FST II; a female patient aged approximately 20: 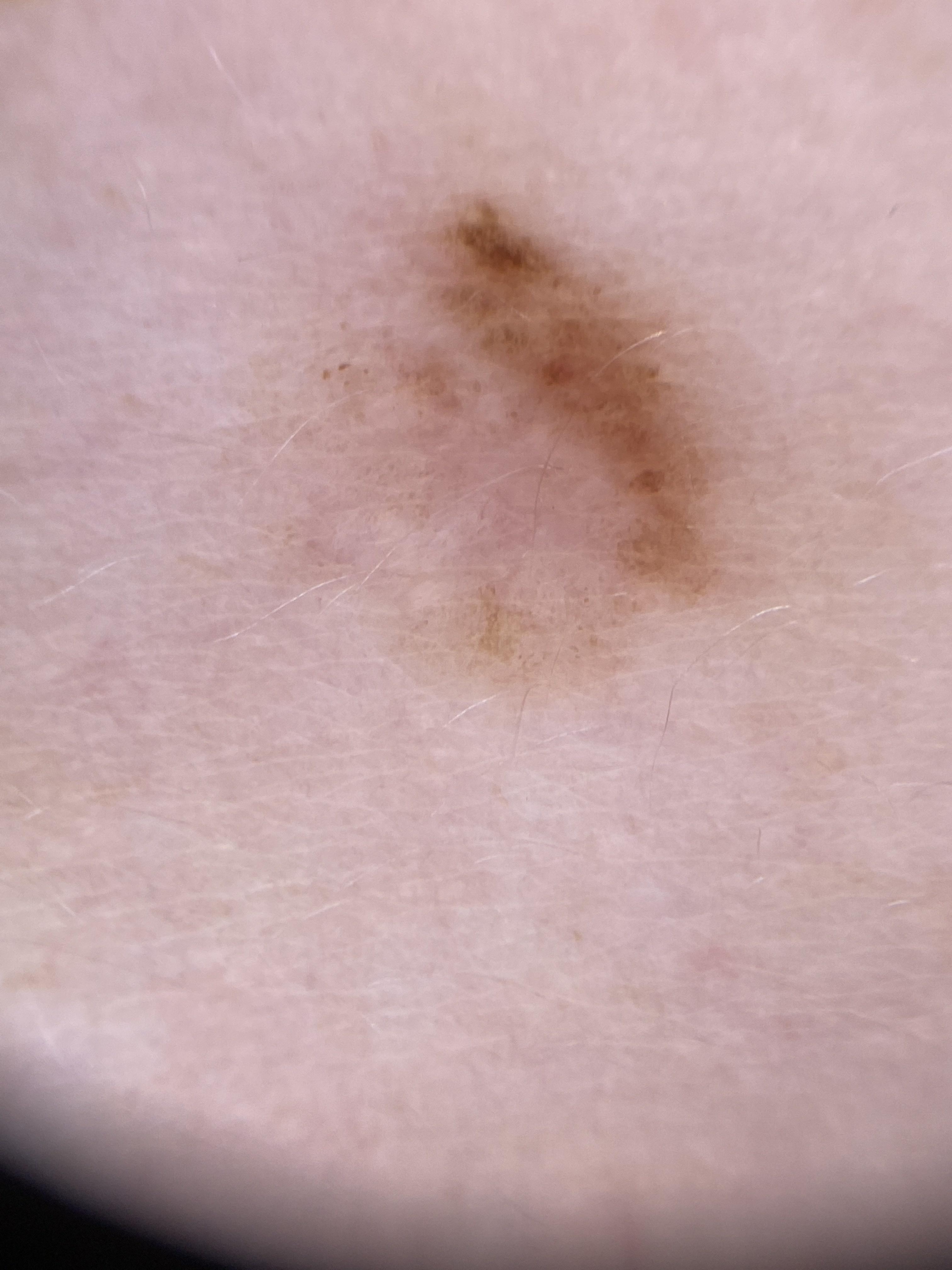  lesion_location:
    region: the trunk
    detail: the posterior trunk
  diagnosis:
    name: Nevus
    malignancy: benign
    confirmation: histopathology
    lineage: melanocytic